Dermoscopy of a skin lesion.
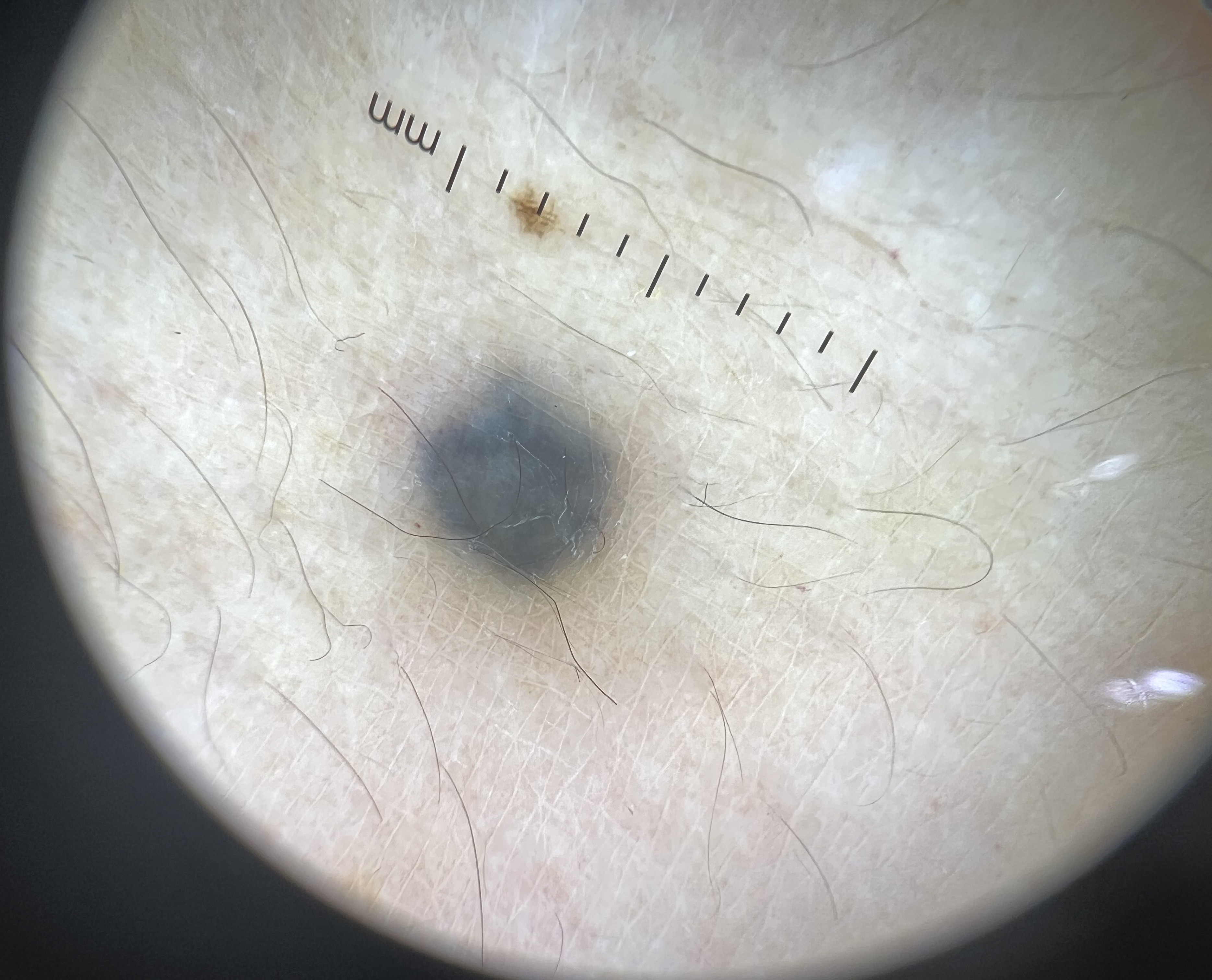Conclusion: Classified as a dermal lesion — a blue nevus.